A dermoscopic photograph of a skin lesion.
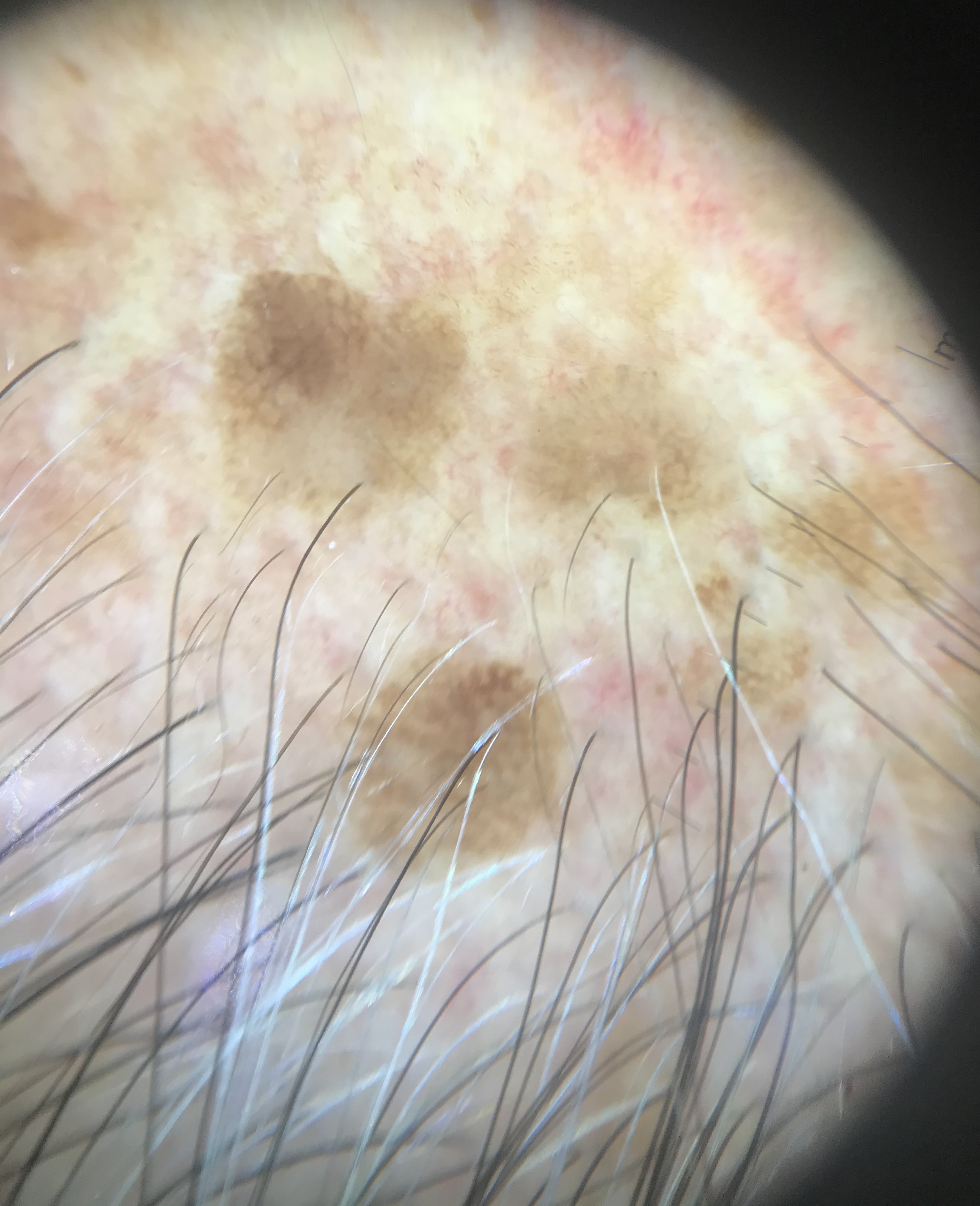Diagnosed as a keratinocytic lesion — a seborrheic keratosis.